A dermoscopic image of a skin lesion:
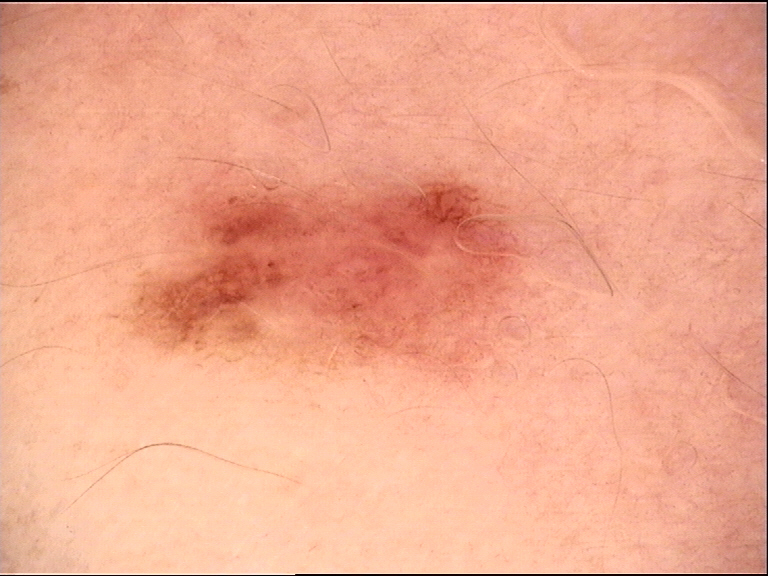assessment: dysplastic junctional nevus (expert consensus).